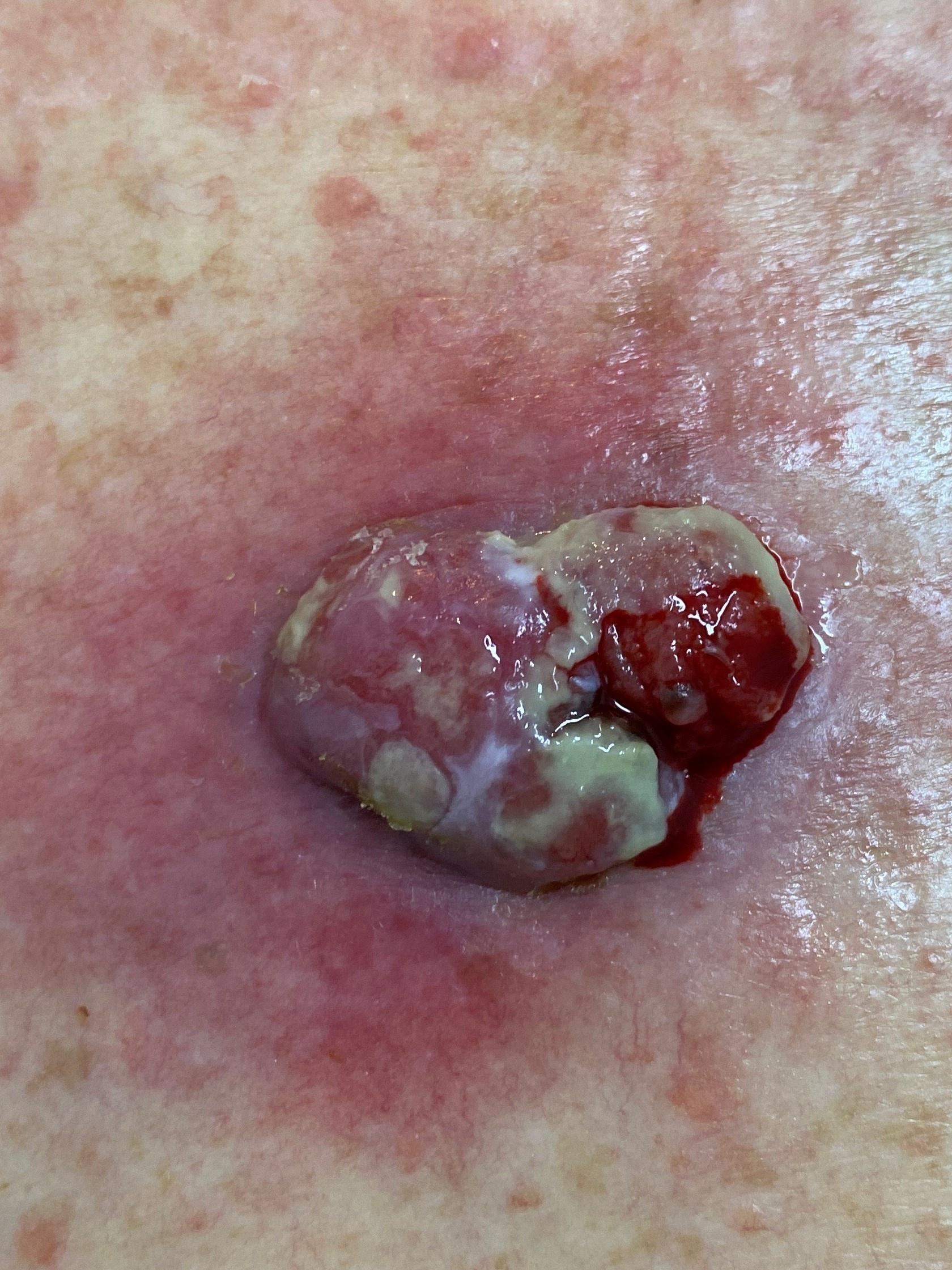pathology — Melanoma (biopsy-proven)